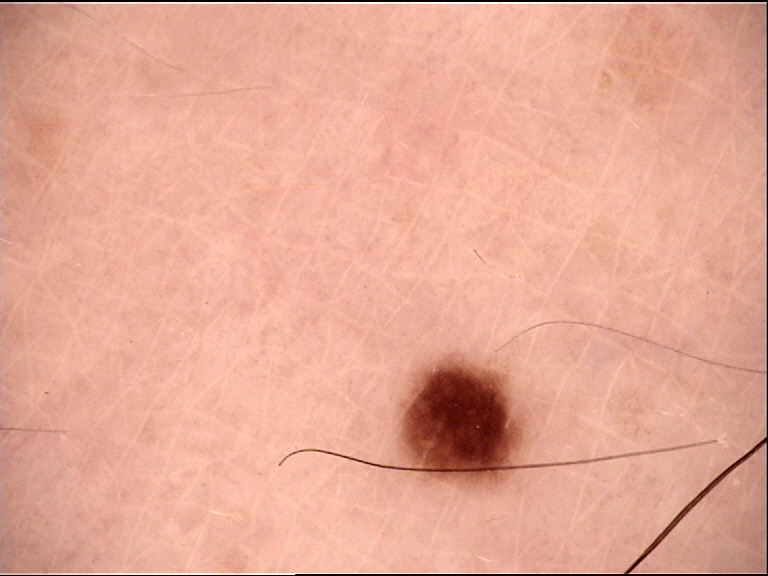A dermatoscopic image of a skin lesion.
The diagnosis was a dysplastic junctional nevus.